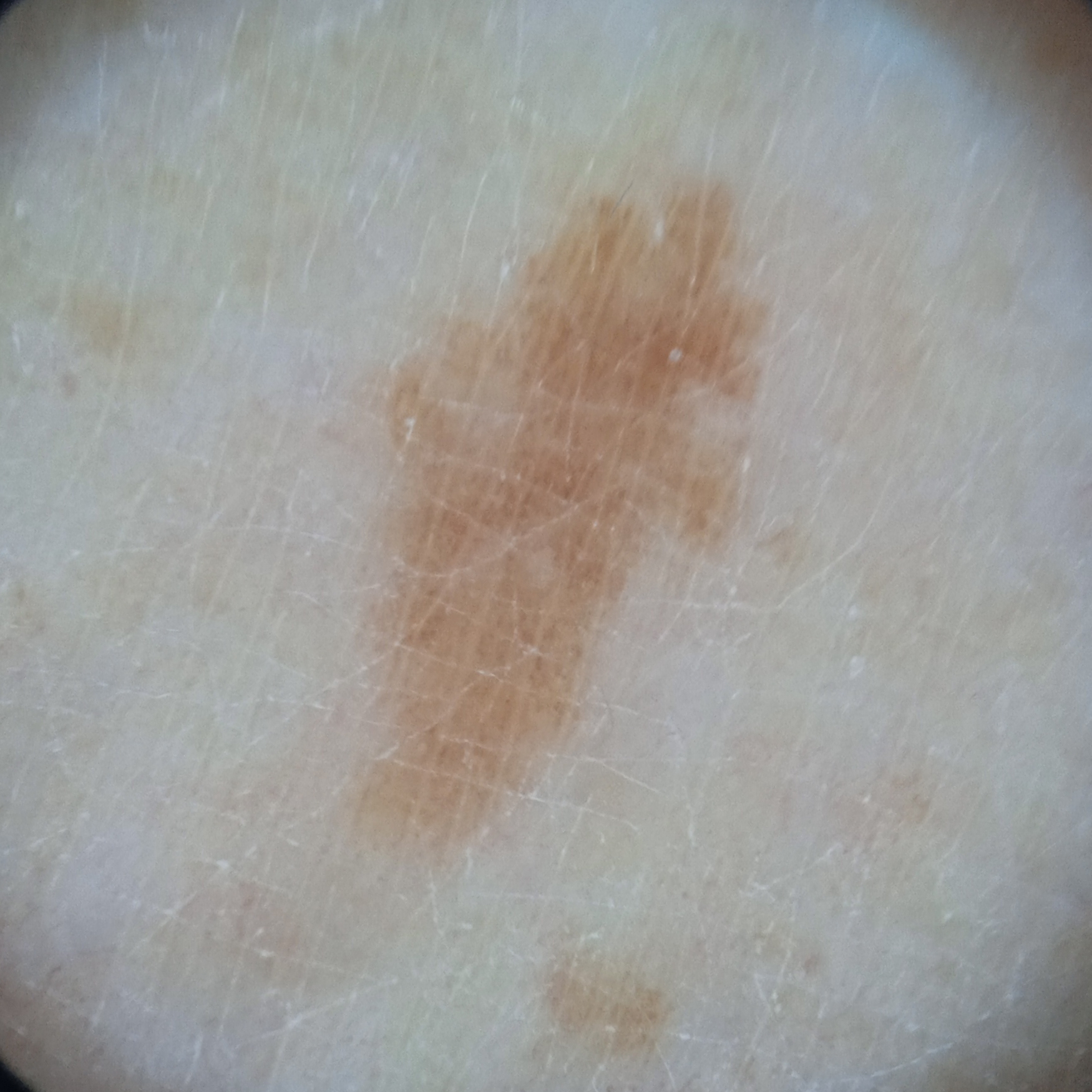Q: What is the referral context?
A: research study (no referral diagnosis)
Q: What is the patient's nevus burden?
A: a moderate number of melanocytic nevi
Q: What is the imaging modality?
A: dermoscopy
Q: What are the relevant risk factors?
A: a personal history of cancer, a personal history of skin cancer
Q: What is the anatomic site?
A: a leg
Q: Lesion size?
A: 8.2 mm
Q: What was the diagnosis?
A: melanocytic nevus (dermatologist consensus)